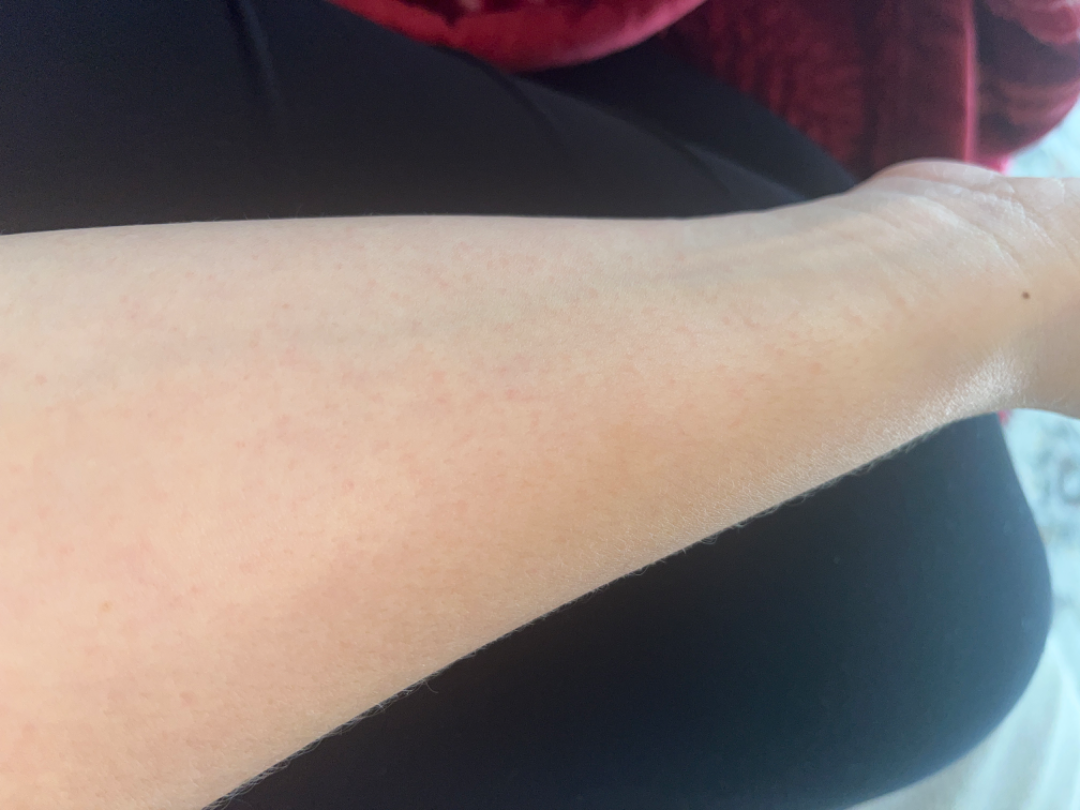Review:
The reviewer was unable to grade this case for skin condition.